A dermoscopic photograph of a skin lesion.
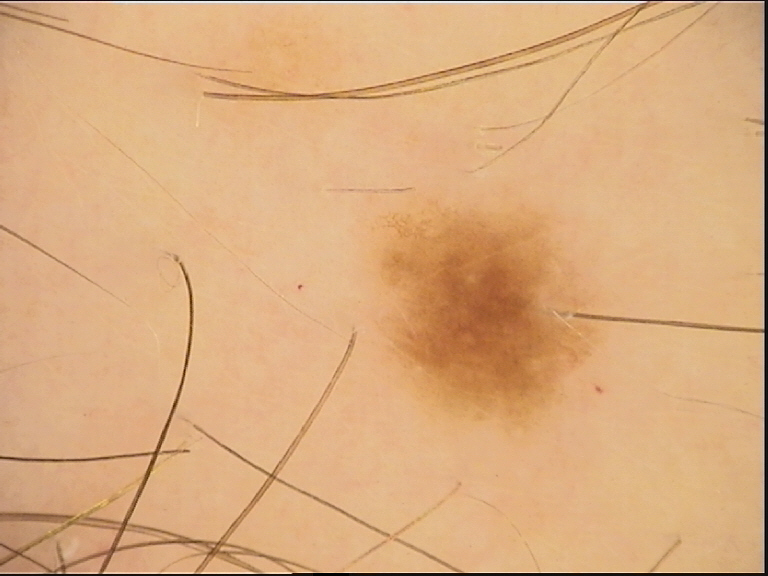| field | value |
|---|---|
| lesion type | banal |
| label | junctional nevus (expert consensus) |